A dermoscopy image of a single skin lesion: 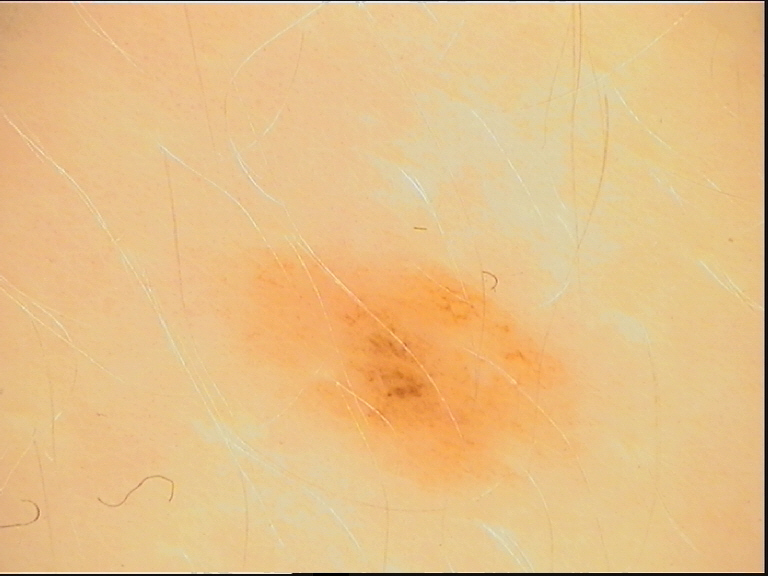Conclusion: Classified as a benign lesion — a dysplastic junctional nevus.